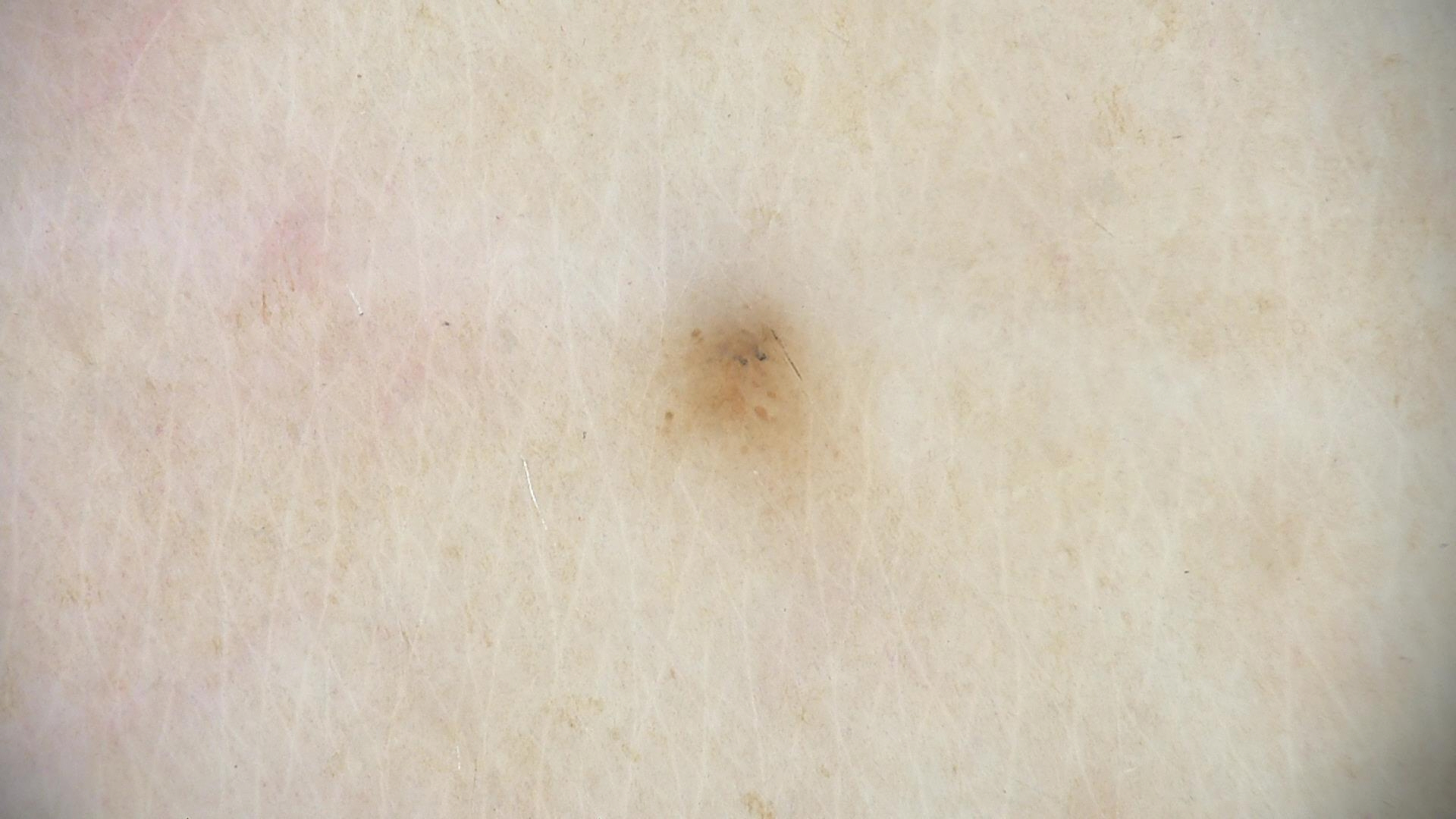Impression: Consistent with a dysplastic junctional nevus.